A dermatoscopic image of a skin lesion:
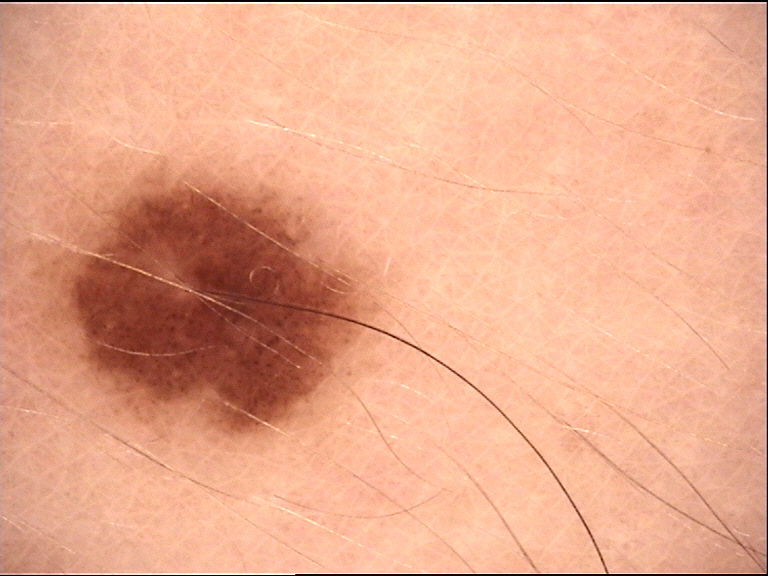Classified as a banal lesion — a junctional nevus.